FST III; a clinical close-up photograph of a skin lesion; a male patient in their 60s.
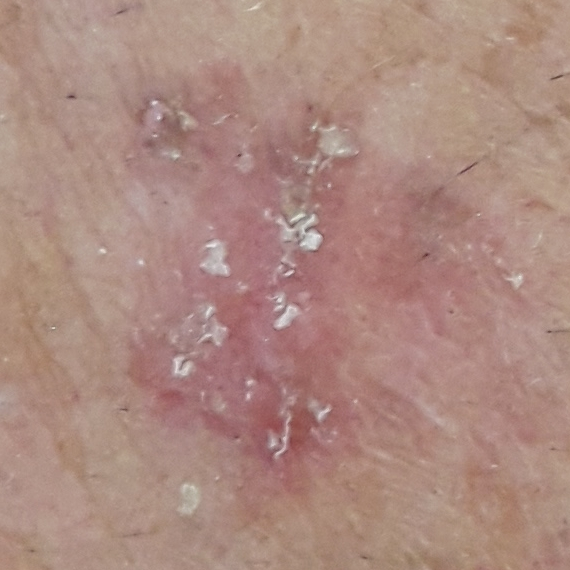{"lesion_location": "a forearm", "lesion_size": {"diameter_1_mm": 20.0, "diameter_2_mm": 13.0}, "symptoms": {"present": ["itching", "bleeding"]}, "diagnosis": {"name": "squamous cell carcinoma", "code": "SCC", "malignancy": "malignant", "confirmation": "histopathology"}}